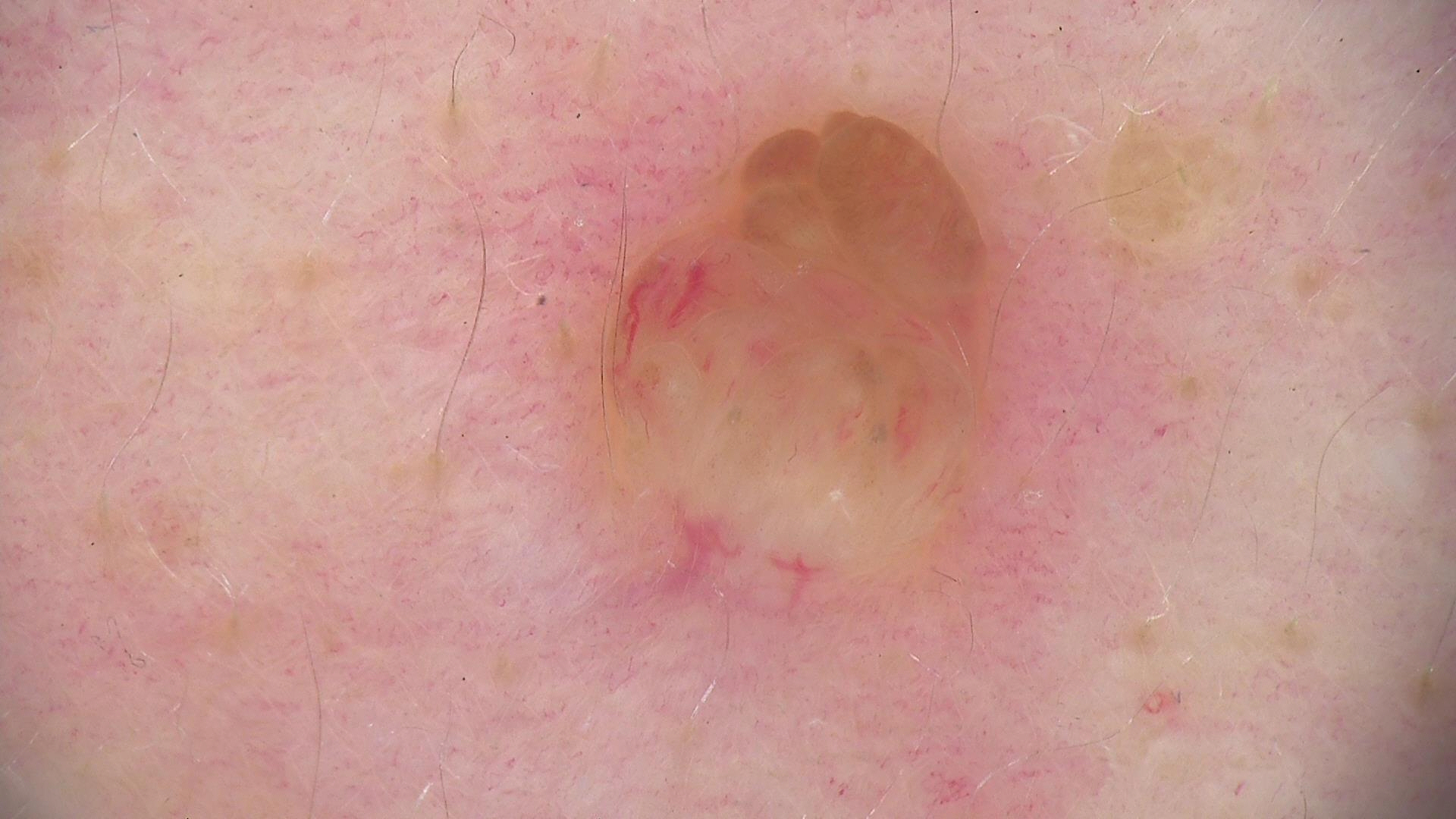{
  "image": "dermatoscopy",
  "diagnosis": {
    "name": "dermal nevus",
    "code": "db",
    "malignancy": "benign",
    "super_class": "melanocytic",
    "confirmation": "expert consensus"
  }
}